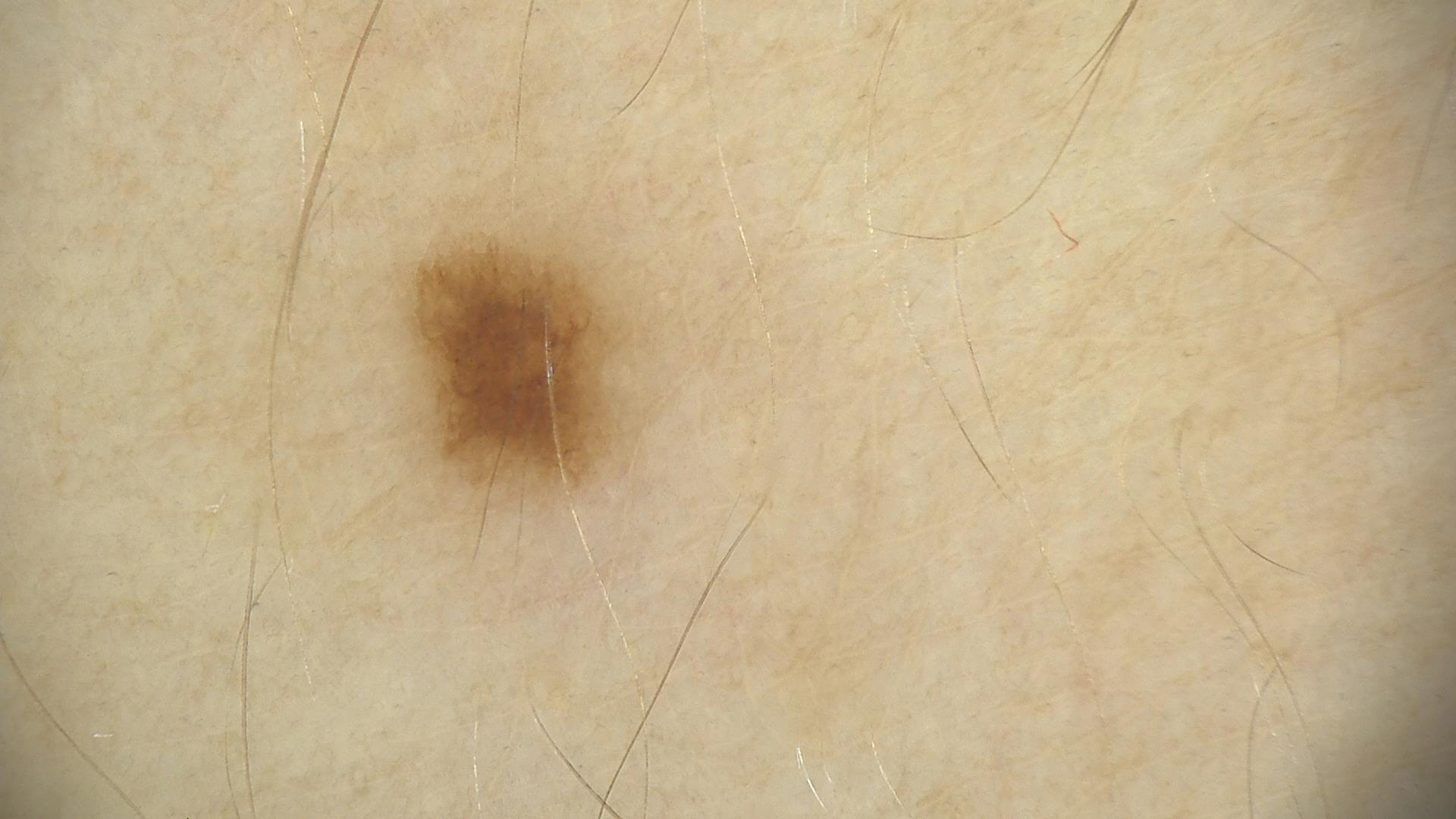A dermatoscopic image of a skin lesion. The diagnostic label was a dysplastic junctional nevus.